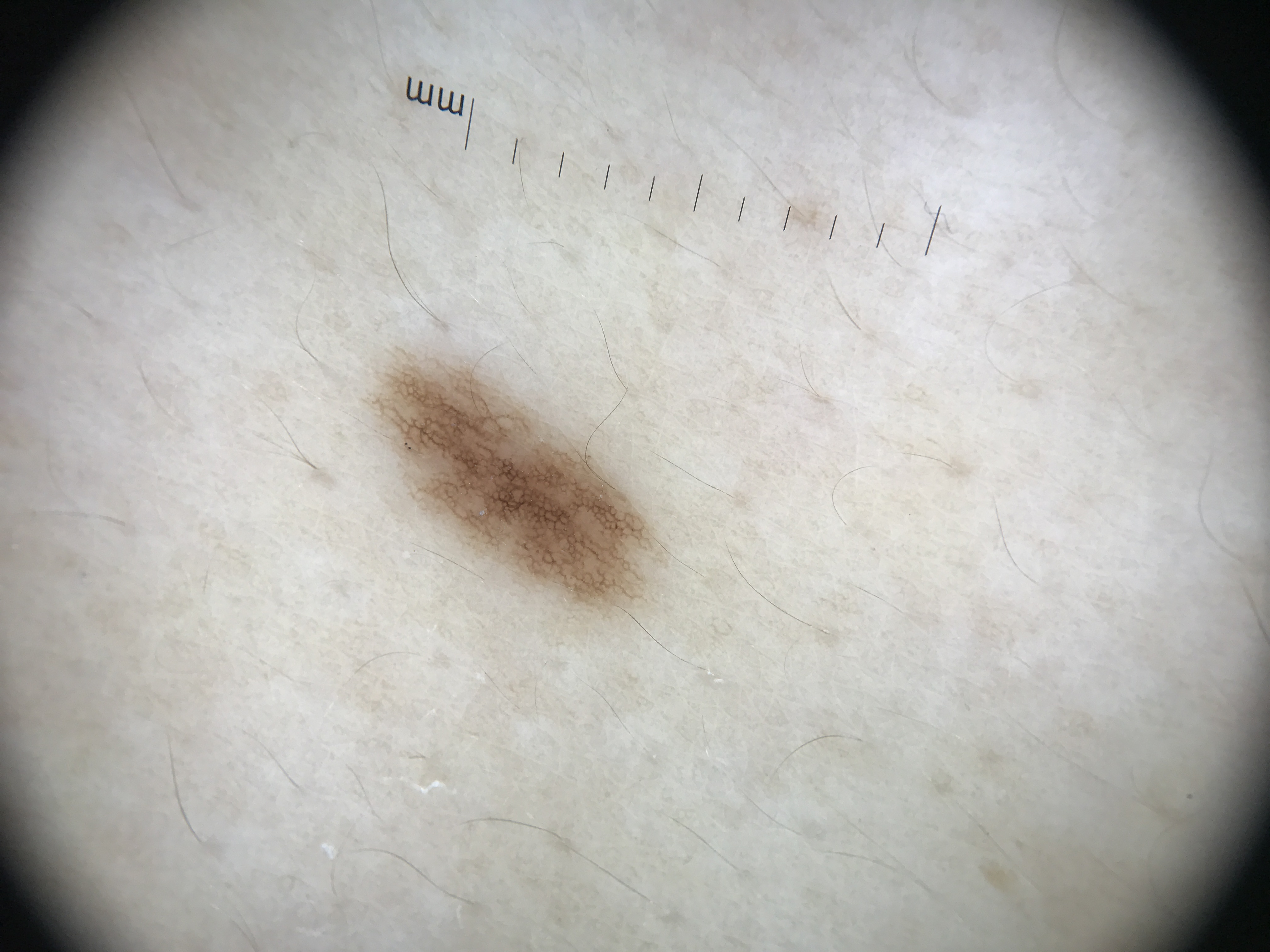A skin lesion imaged with a dermatoscope. The diagnostic label was a dysplastic junctional nevus.